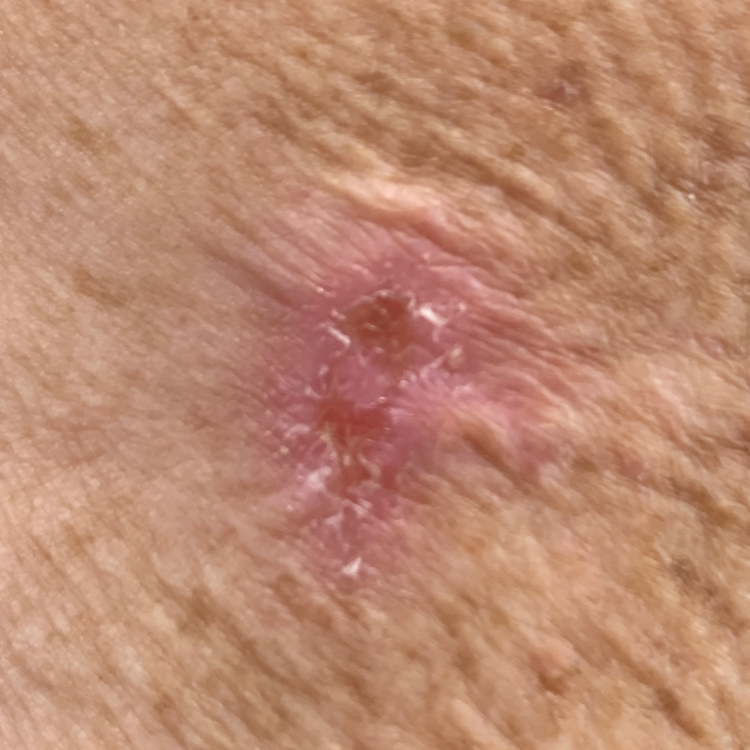History notes prior skin cancer (patient or family), prior malignancy (patient or family), no alcohol use, and no tobacco use. A clinical close-up photograph of a skin lesion. A female patient 59 years of age. FST II. Located on an arm. Per patient report, the lesion has bled, has grown, and itches. Histopathologically confirmed as a basal cell carcinoma.